A skin lesion imaged with a dermatoscope: 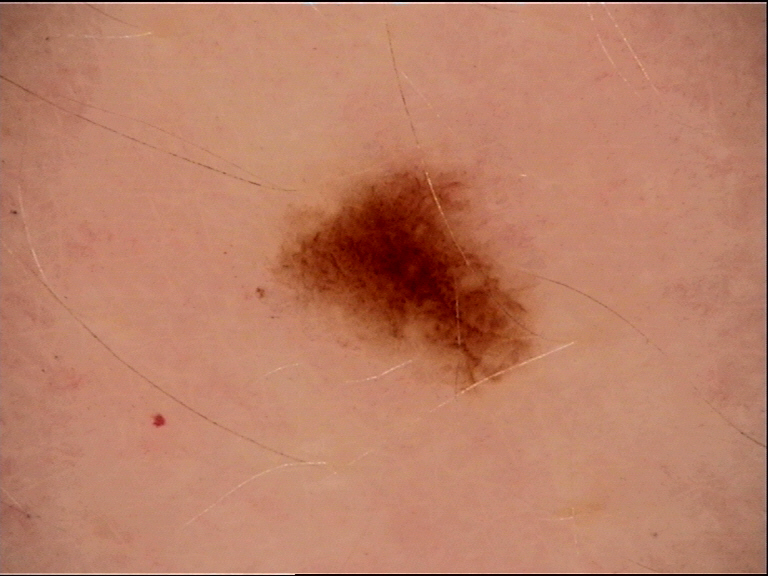The diagnosis was a benign lesion — a dysplastic junctional nevus.